This is a close-up image — 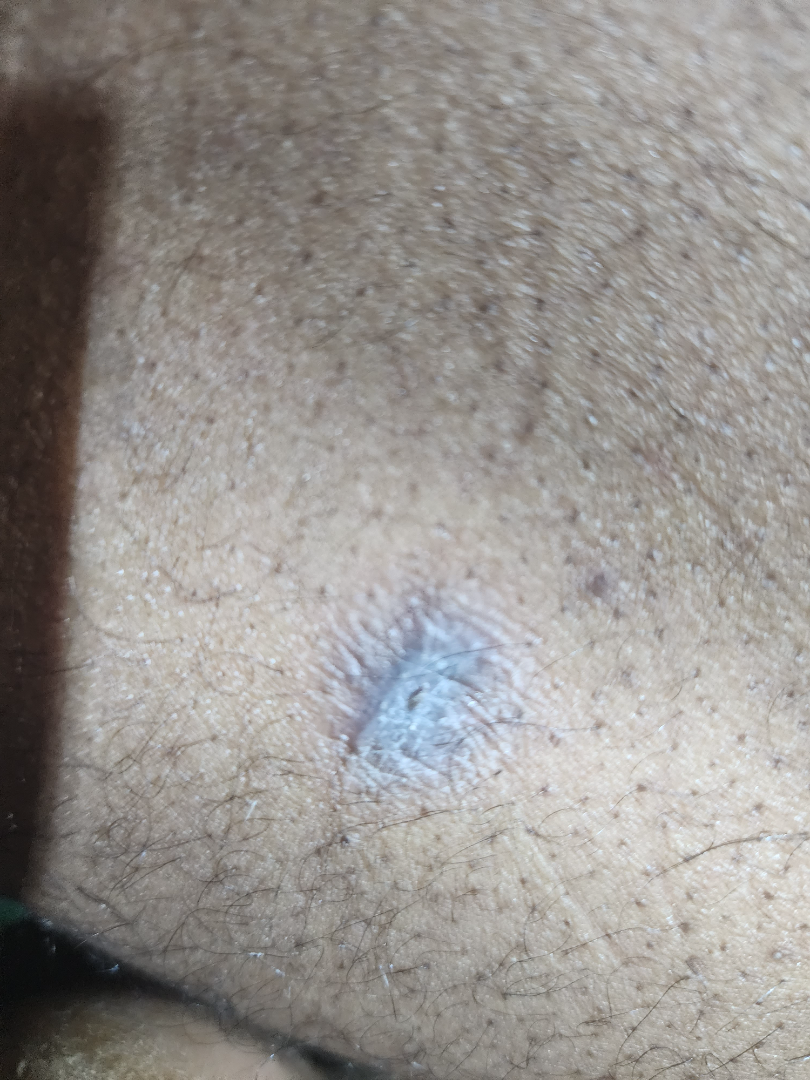Findings:
• skin tone · Fitzpatrick phototype IV
• diagnostic considerations · Scar Condition (primary)